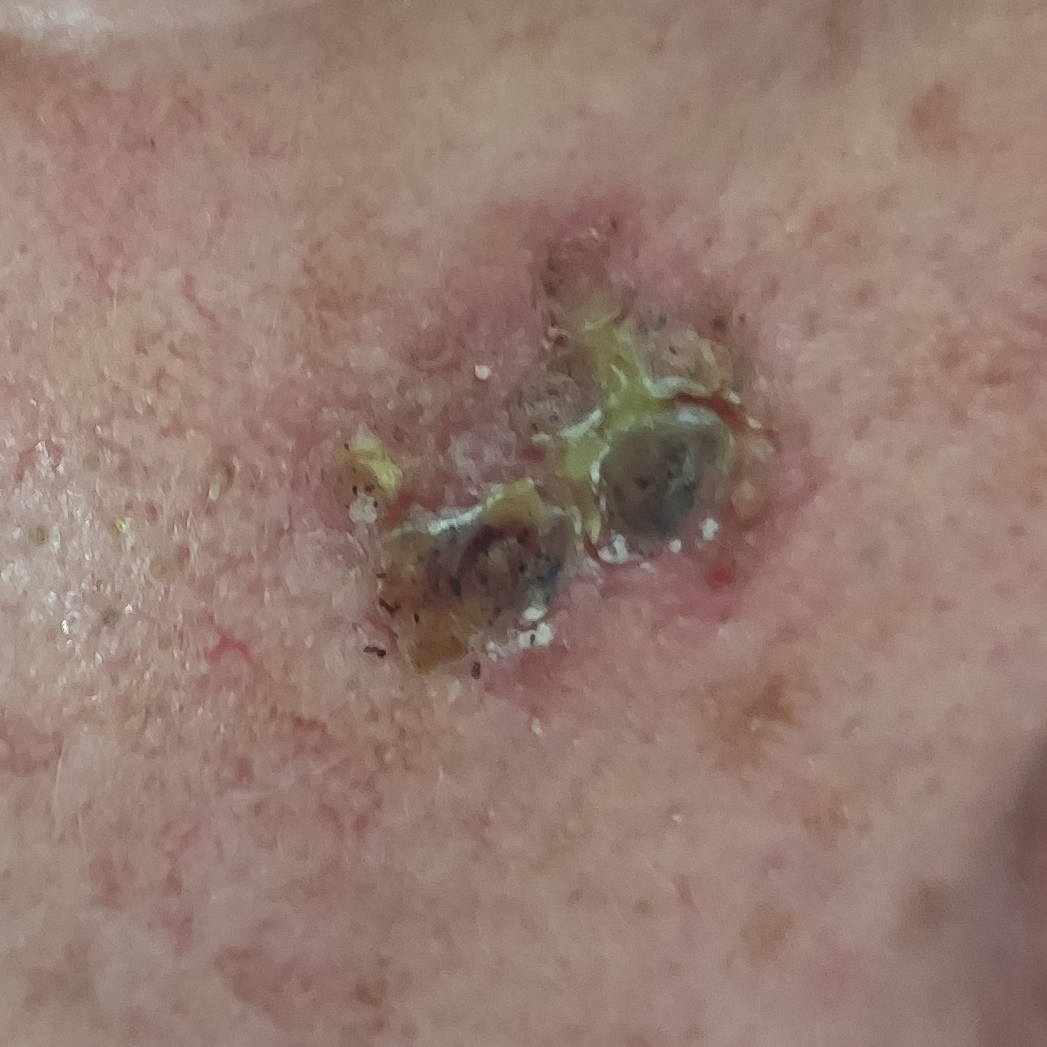– skin phototype — III
– exposure history — alcohol use, pesticide exposure, prior skin cancer (patient or family), prior malignancy (patient or family), tobacco use
– subject — male, 32 years old
– anatomic site — the face
– diagnosis — squamous cell carcinoma (biopsy-proven)